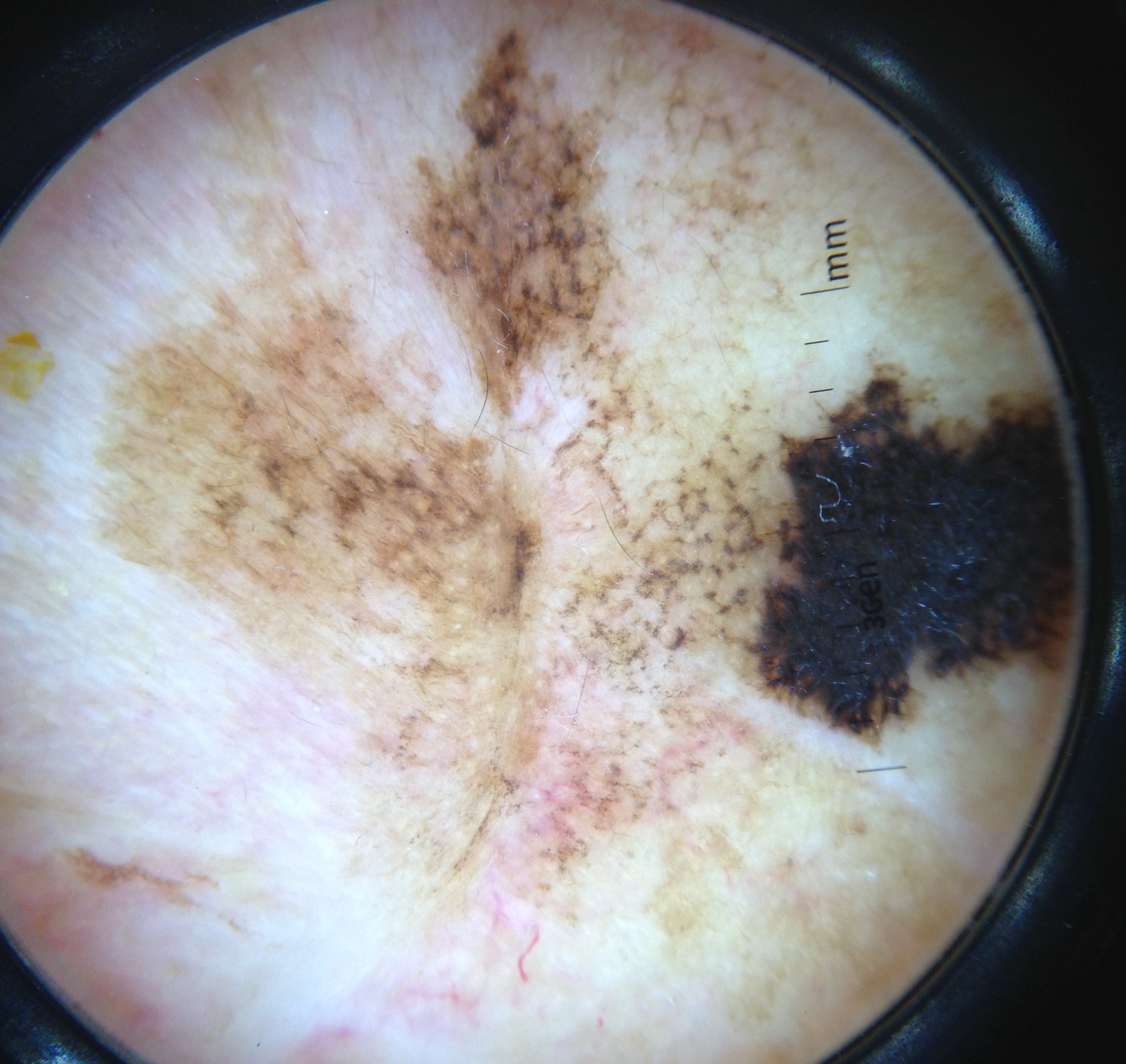image type: dermoscopy | class: lentigo maligna (biopsy-proven).